A dermoscopic image of a skin lesion; the patient says their skin tans without first burning; a male subject 79 years of age; acquired for a research image collection, with no referral diagnosis:
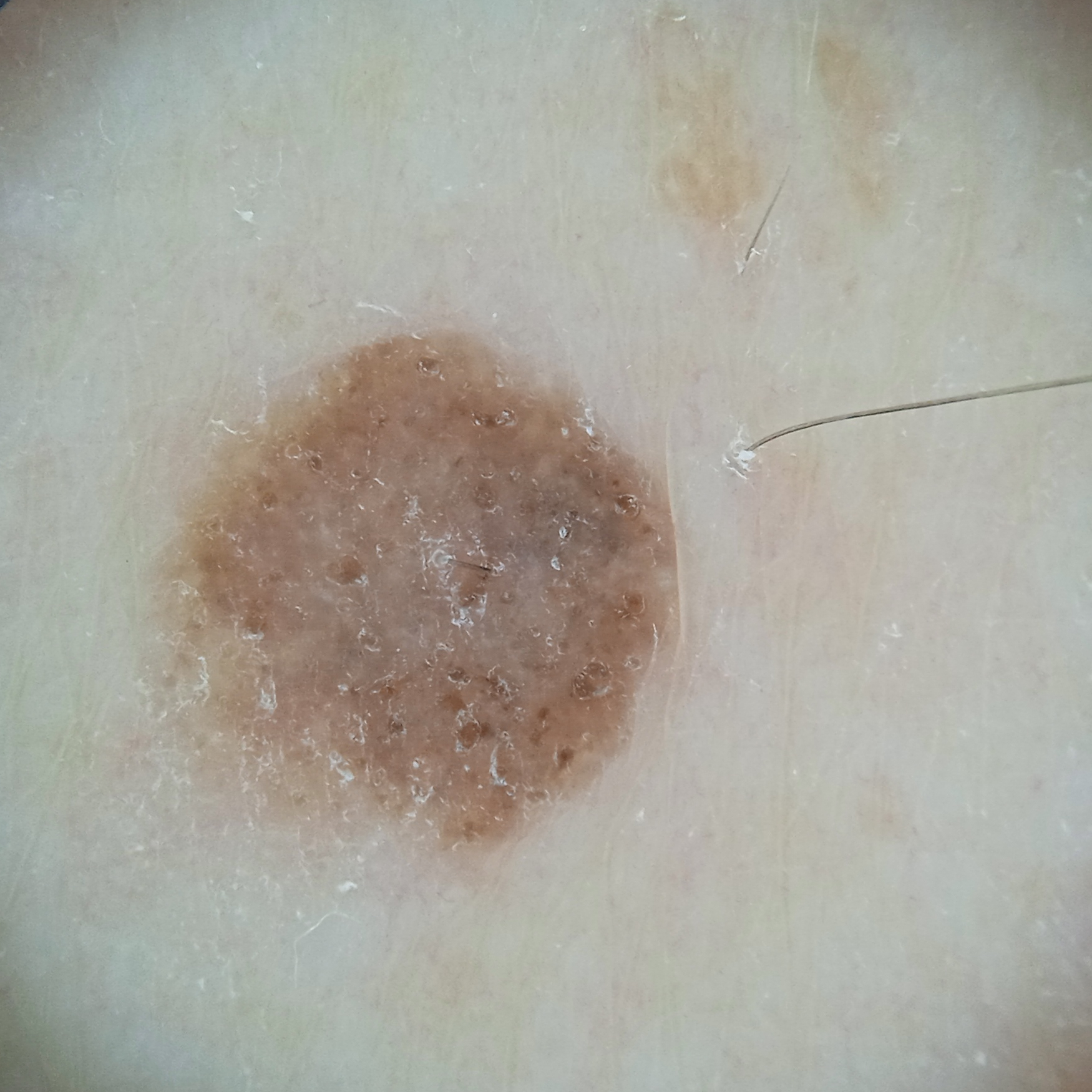Q: Lesion size?
A: 5.8 mm
Q: What was the diagnosis?
A: melanocytic nevus (dermatologist consensus)